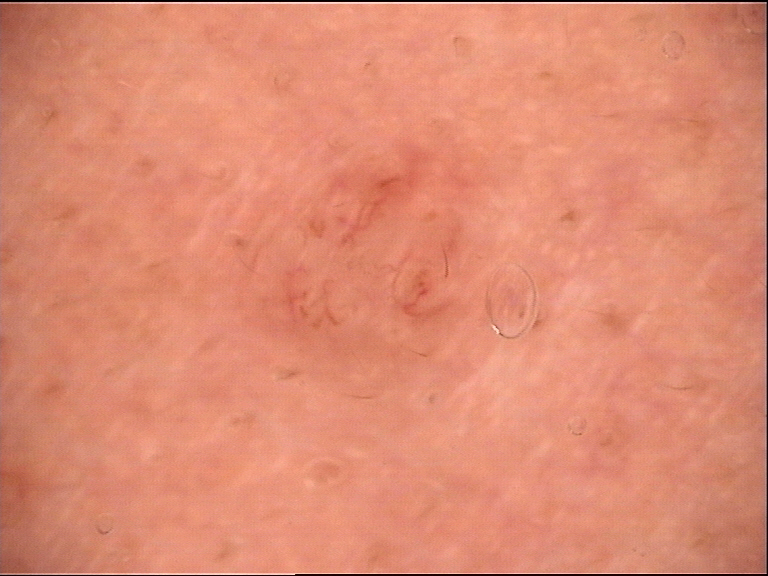Diagnosed as a dermal nevus.